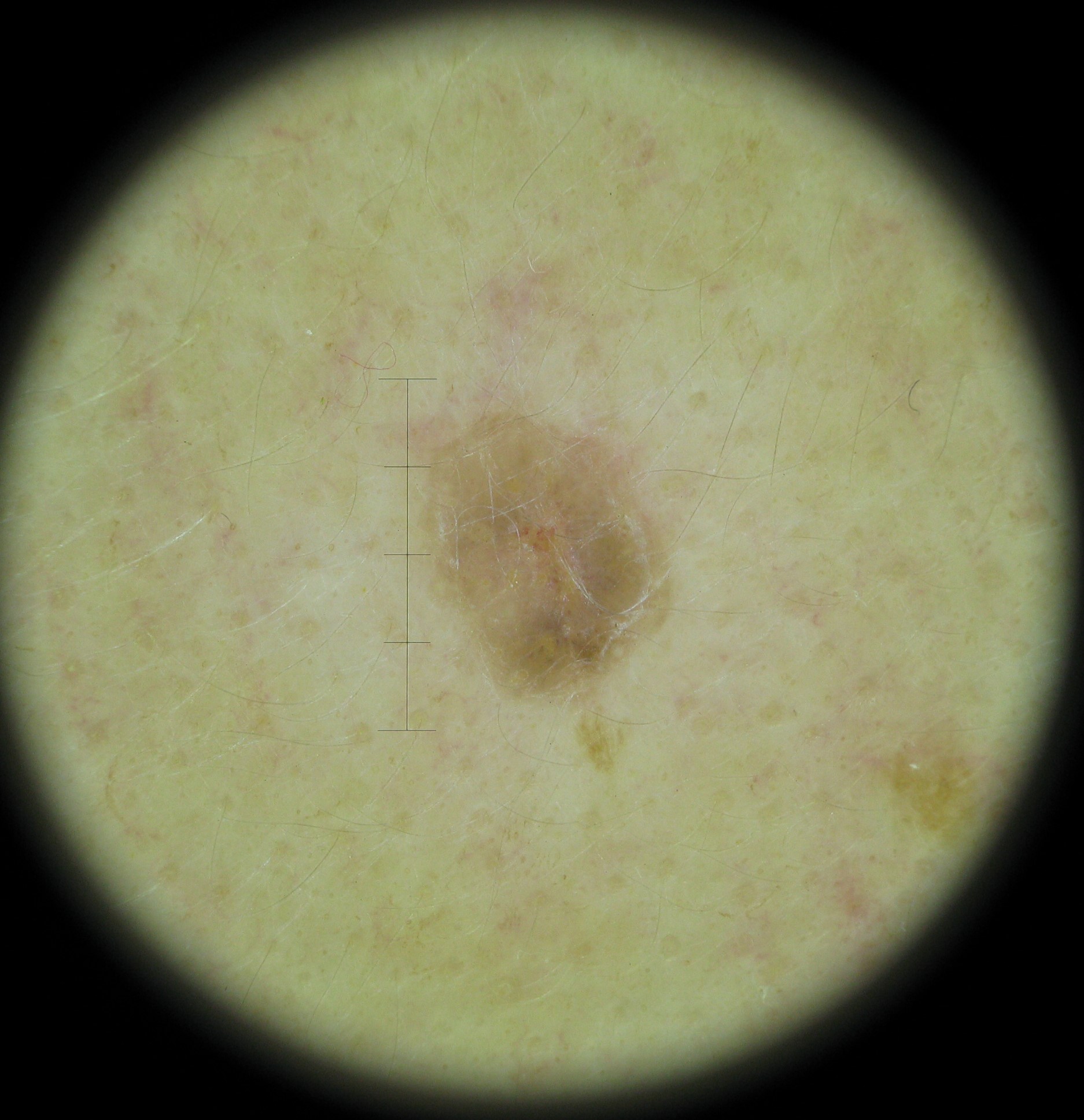A dermoscopic image of a skin lesion. This is a keratinocytic lesion. Consistent with a benign lesion — a seborrheic keratosis.